The chart records pesticide exposure, no prior skin cancer (patient or family), and no tobacco use · a male patient in their late 60s · the patient was assessed as FST II.
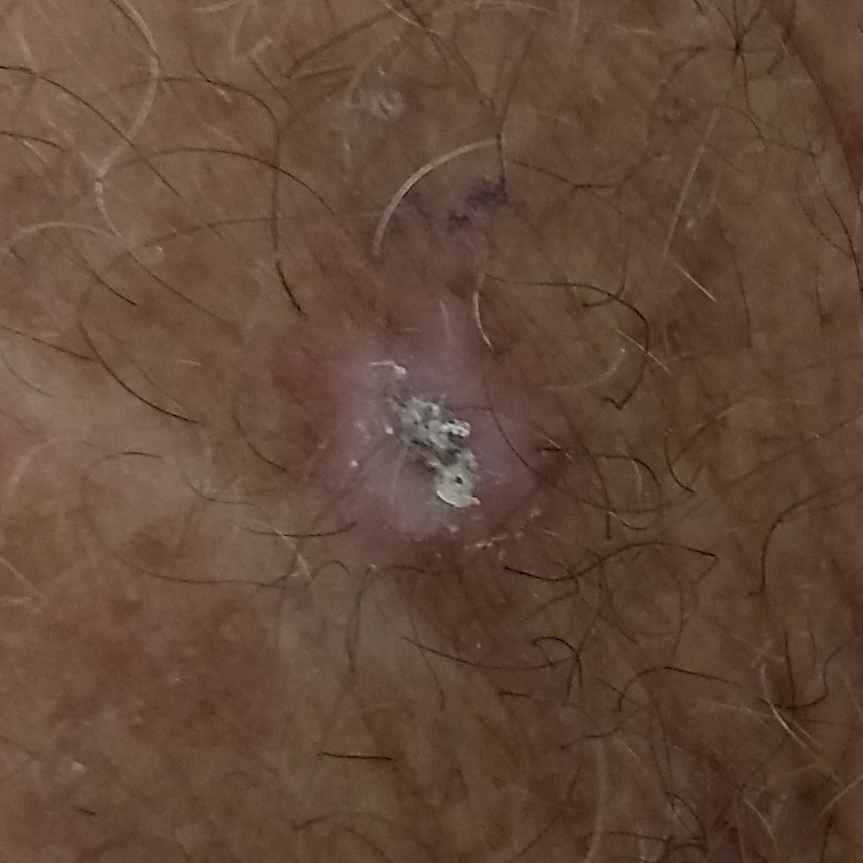* anatomic site: a forearm
* lesion diameter: approx. 10 × 10 mm
* patient-reported symptoms: growth, bleeding, elevation, itching / no pain
* diagnosis: actinic keratosis (biopsy-proven)